The top or side of the foot is involved, the patient is a female aged 60–69, a close-up photograph: 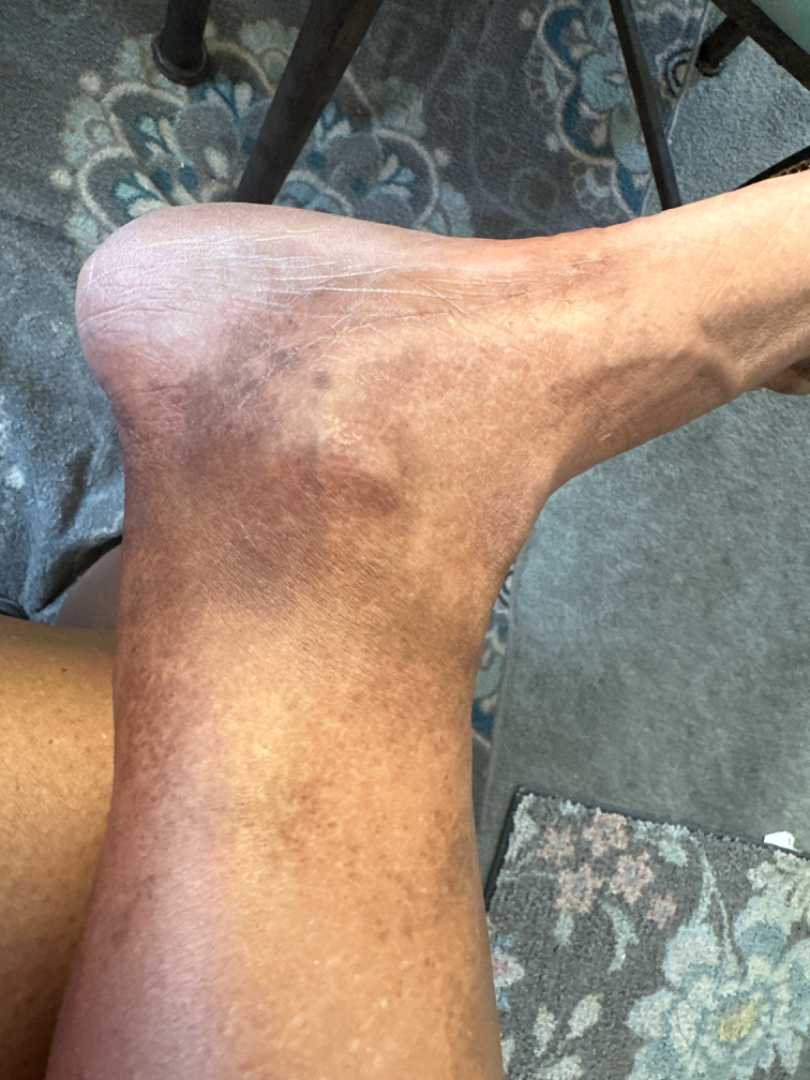On photographic review by a dermatologist: the differential includes Pigmented purpuric eruption, Post-Inflammatory hyperpigmentation and Drug induced abnormal pigmentation of skin, with no clear leading consideration.